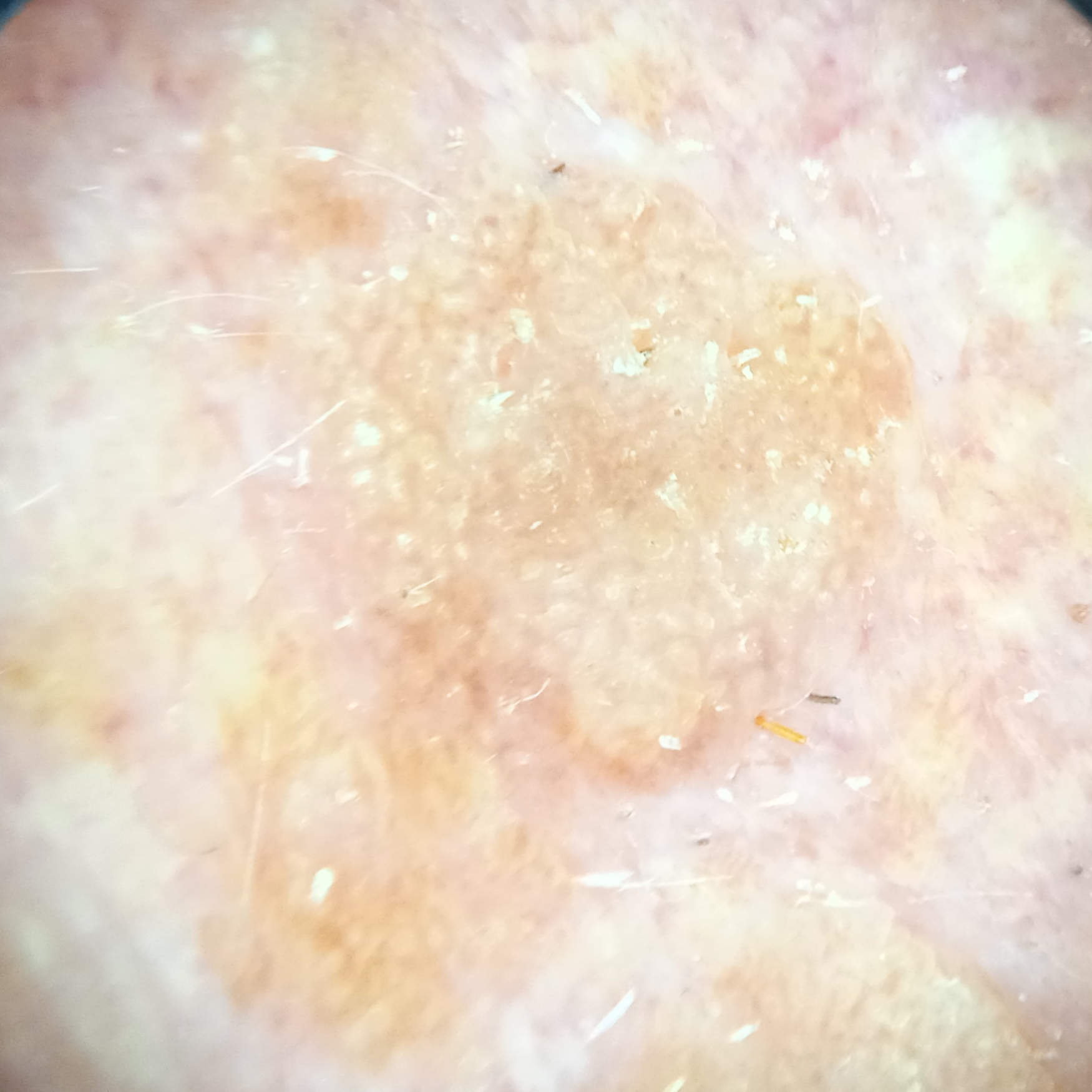clinical context = research study (no referral diagnosis)
modality = dermoscopic image
nevus count = few melanocytic nevi overall
sun reaction = skin reddens with sun exposure
lesion size = 7.5 mm
assessment = seborrheic keratosis (dermatologist consensus)